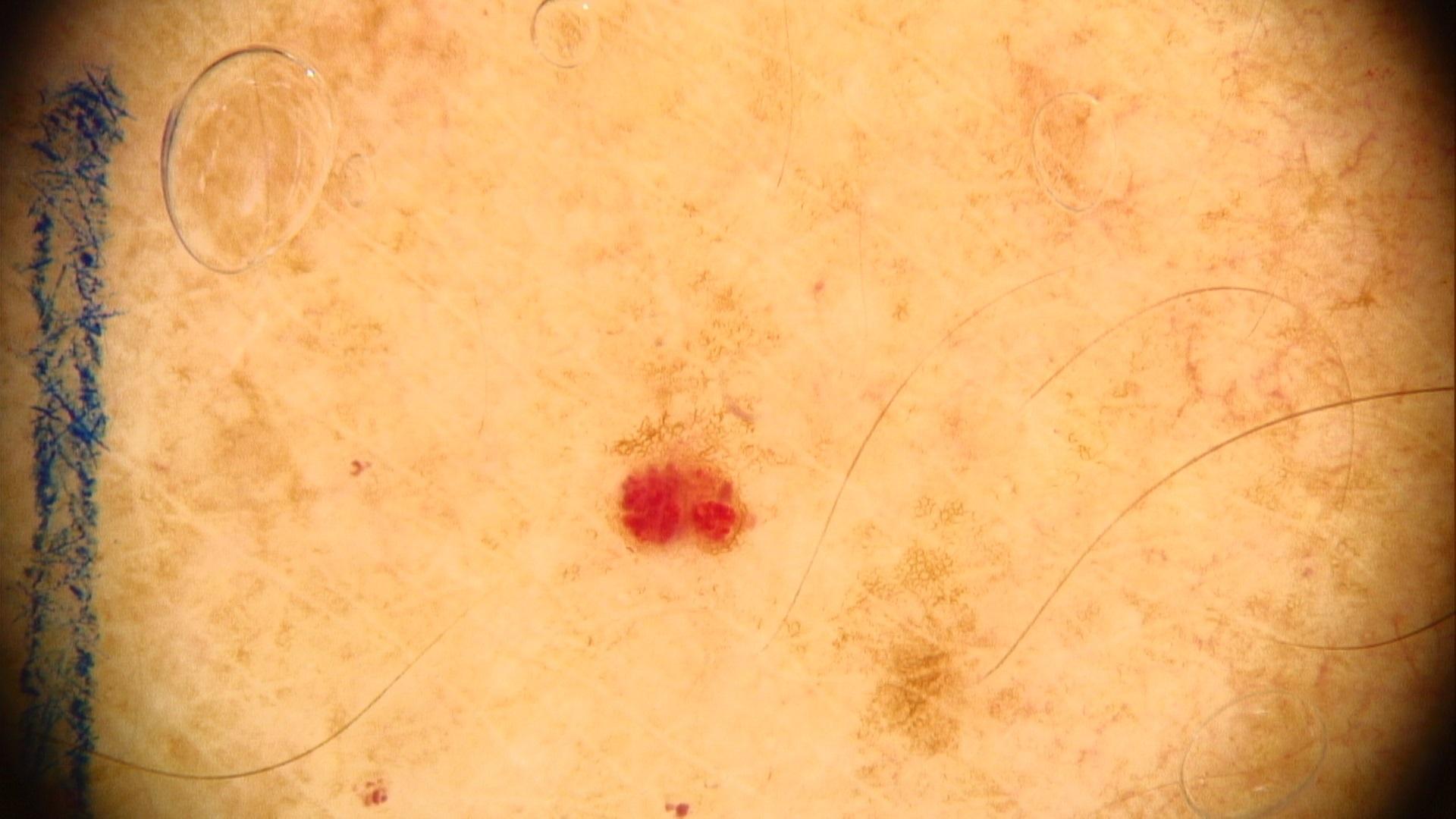A skin lesion imaged with a dermatoscope. The lesion is on an upper extremity. Consistent with a vascular lesion.